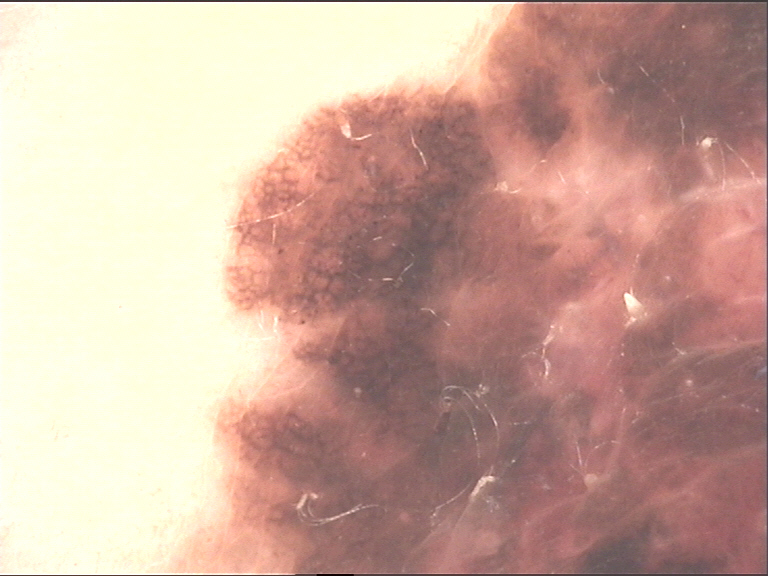Case:
* class: melanoma (biopsy-proven)